Dermoscopy of a skin lesion.
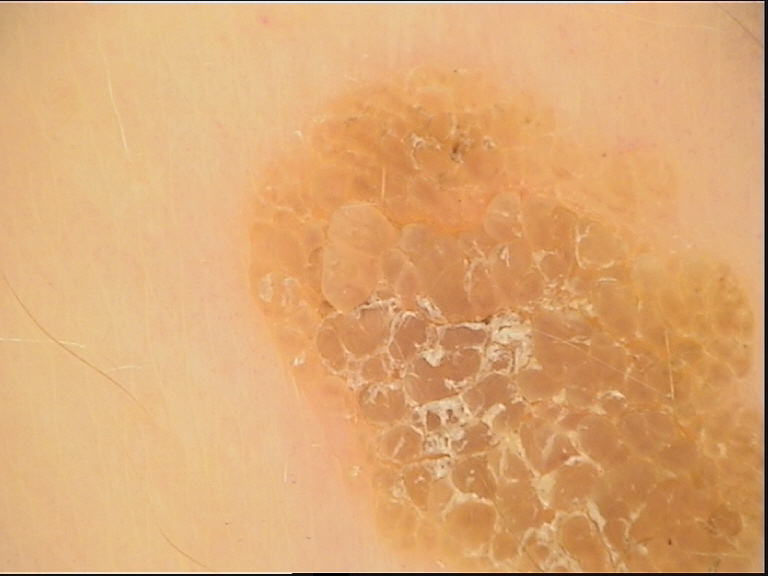diagnosis=seborrheic keratosis (expert consensus).